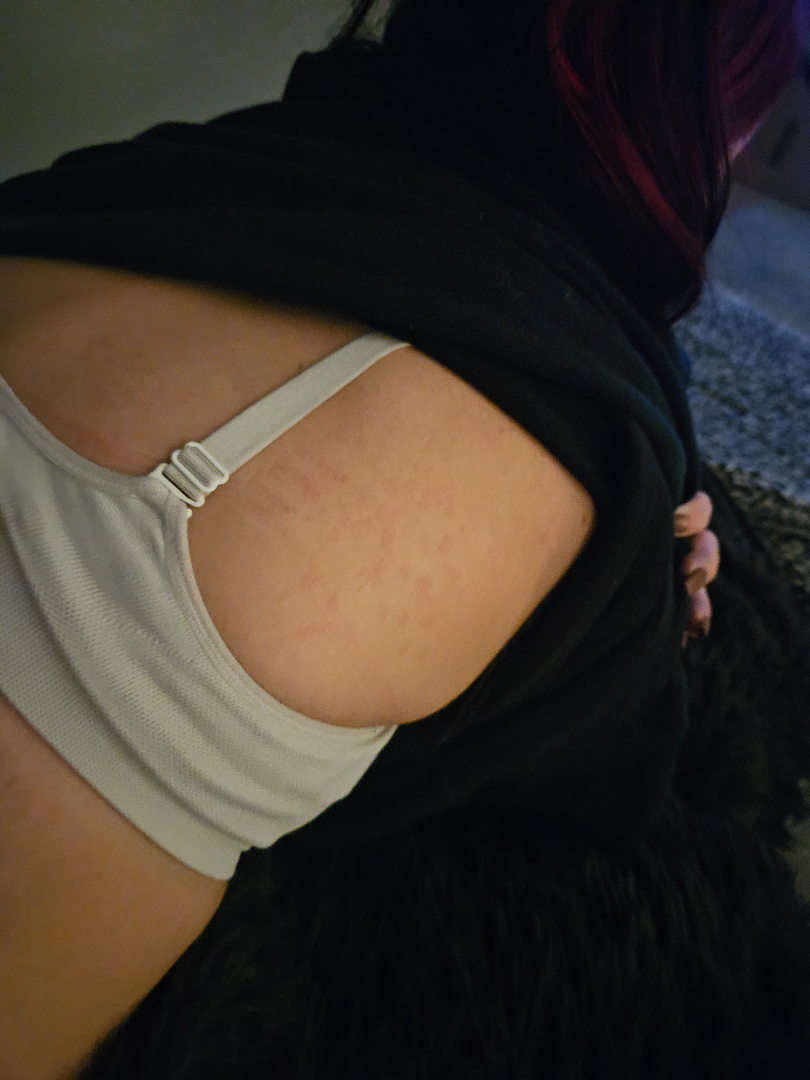Most likely Tinea Versicolor; the differential also includes Post-Inflammatory hyperpigmentation.